A skin lesion imaged with a dermatoscope:
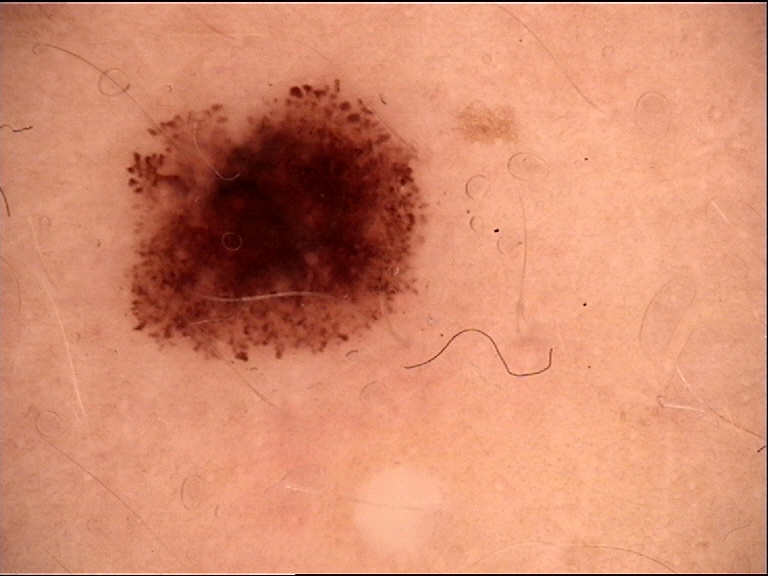diagnostic label: dysplastic junctional nevus (expert consensus).